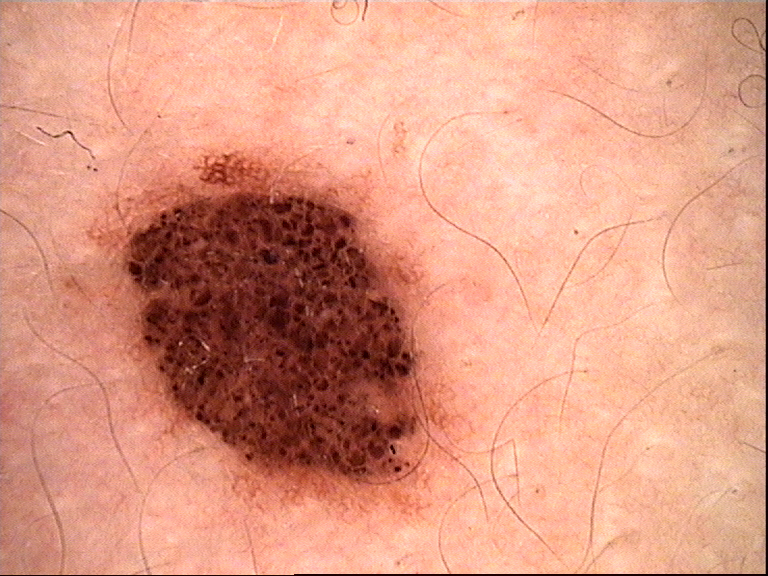Findings:
– diagnosis: dysplastic compound nevus (expert consensus)